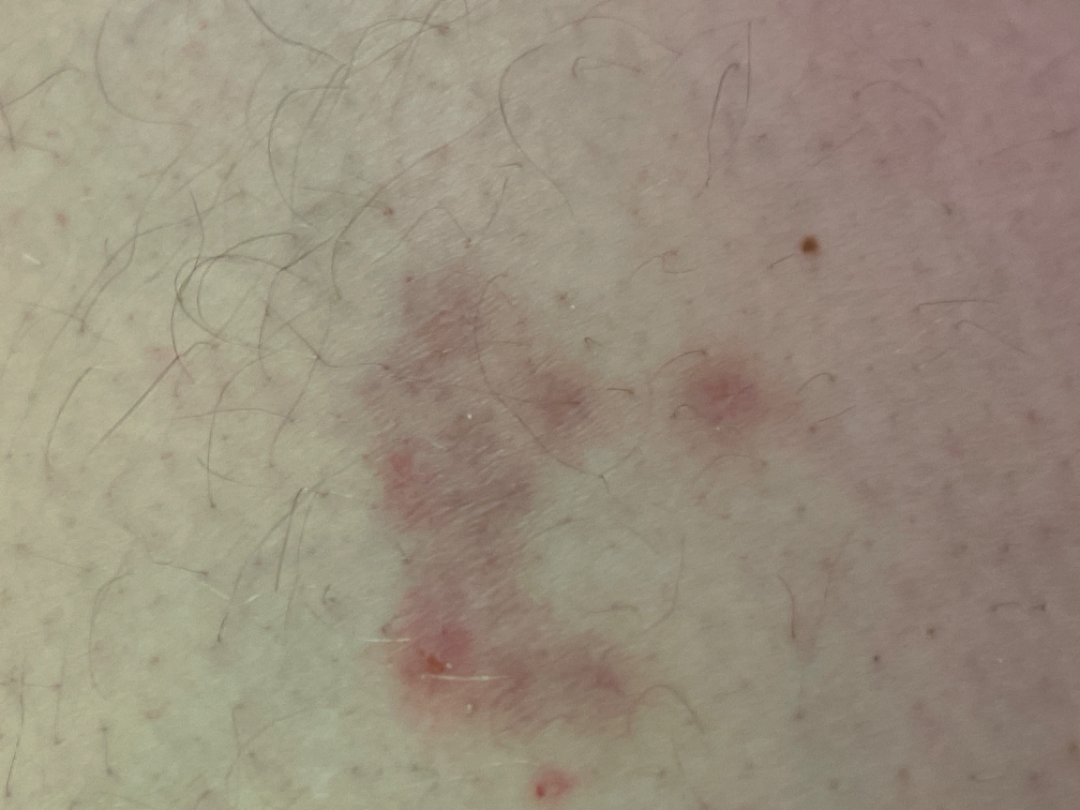assessment = the leading consideration is Herpes Simplex; the differential also includes Eczema; less likely is Insect Bite.